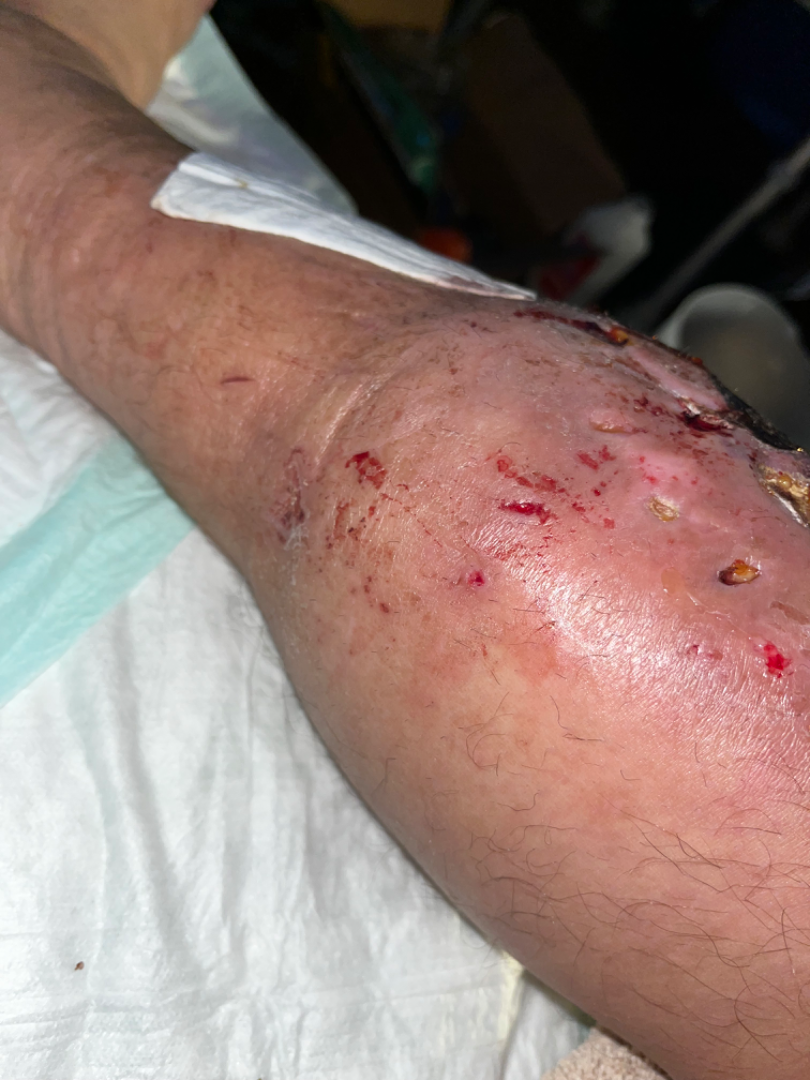On photographic review, the favored diagnosis is Inflicted skin lesions.